The patient considered this a rash. Non-clinician graders estimated 2 on the Monk skin tone scale. The contributor is 18–29, female. Located on the leg. The contributor reports the lesion is raised or bumpy. Reported lesion symptoms include itching, pain and burning. A close-up photograph.
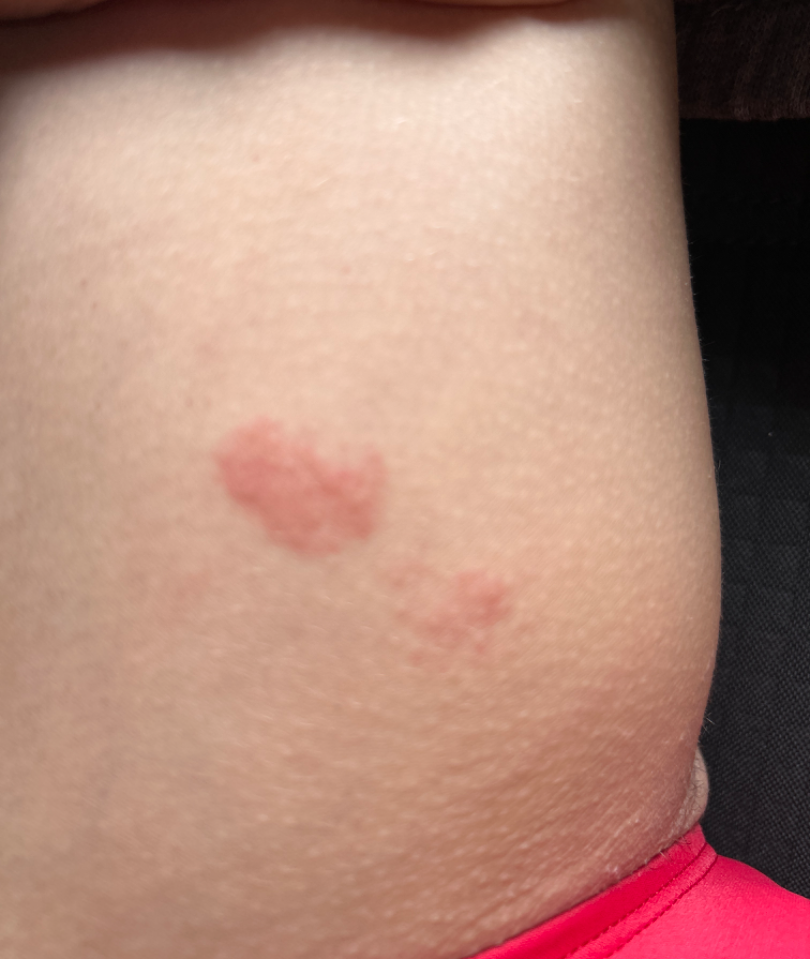assessment = ungradable on photographic review.